A female patient aged 68-72. A clinical photograph of a skin lesion.
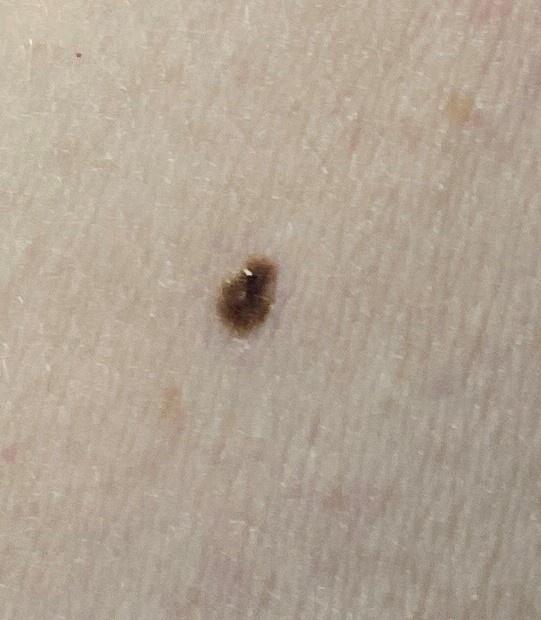impression = Nevus.